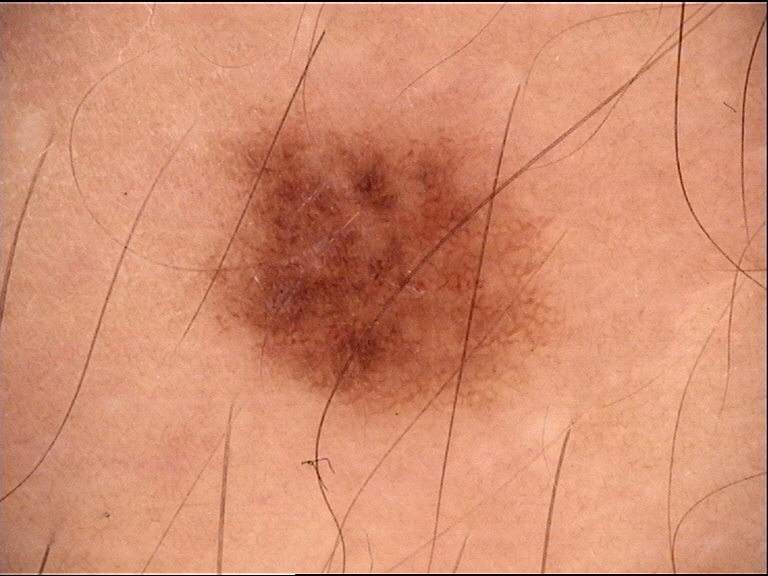A dermoscopic close-up of a skin lesion. Diagnosed as a benign lesion — a dysplastic junctional nevus.